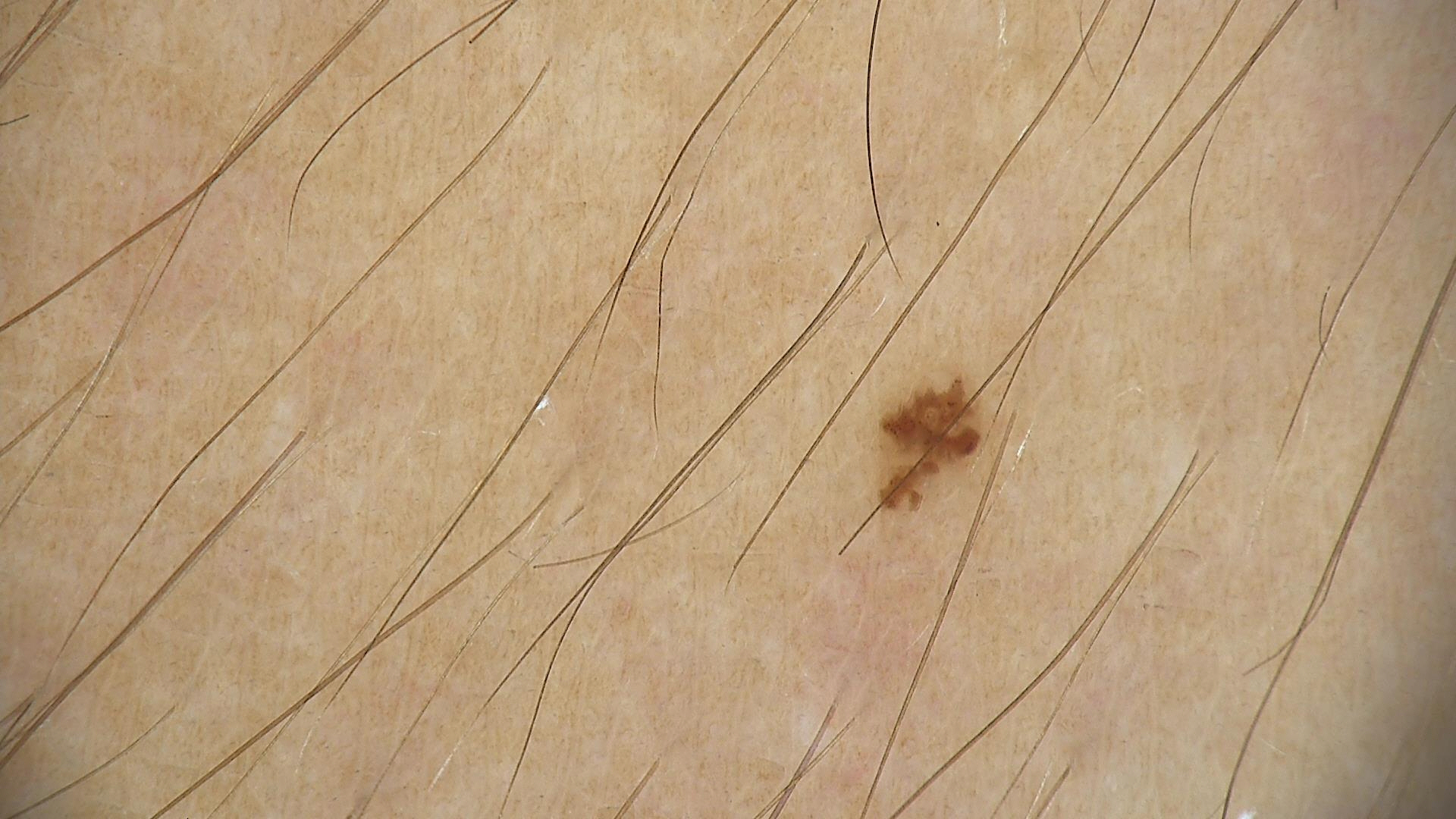Consistent with a dysplastic junctional nevus.